The patient says their skin reddens with sun exposure; collected as part of a research study, without a referral diagnosis; a macroscopic clinical photograph of a skin lesion; a male patient aged 77:
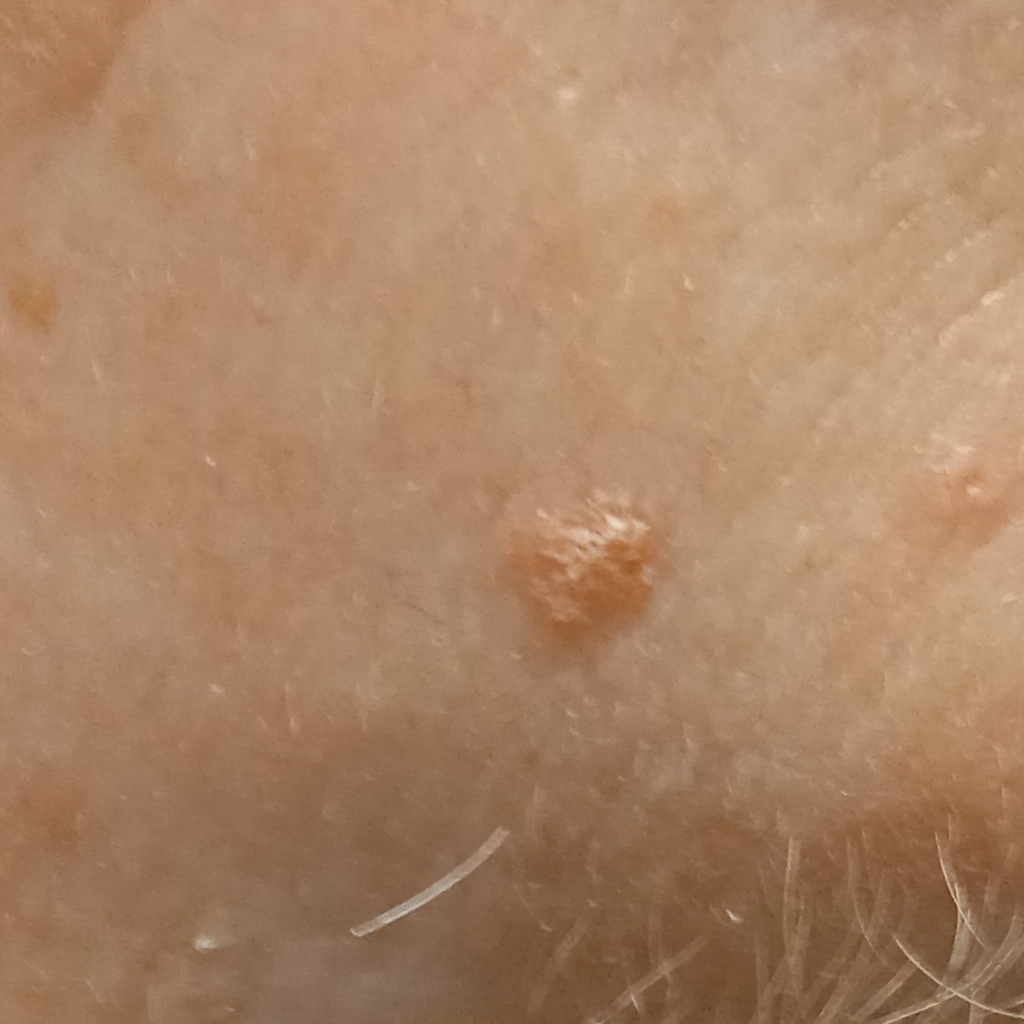Dermatologist review favored an actinic keratosis.